Close-up view:
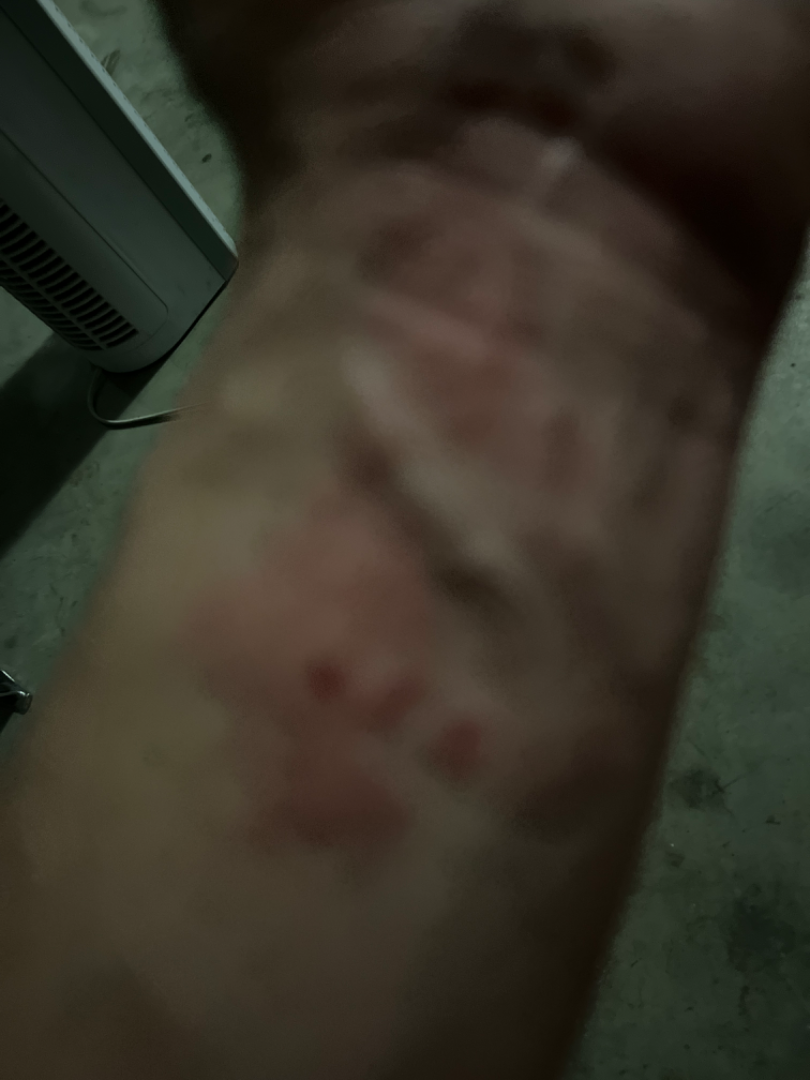The image was not sufficient for the reviewer to characterize the skin condition.